A clinical photograph showing a skin lesion; a subject in their 60s.
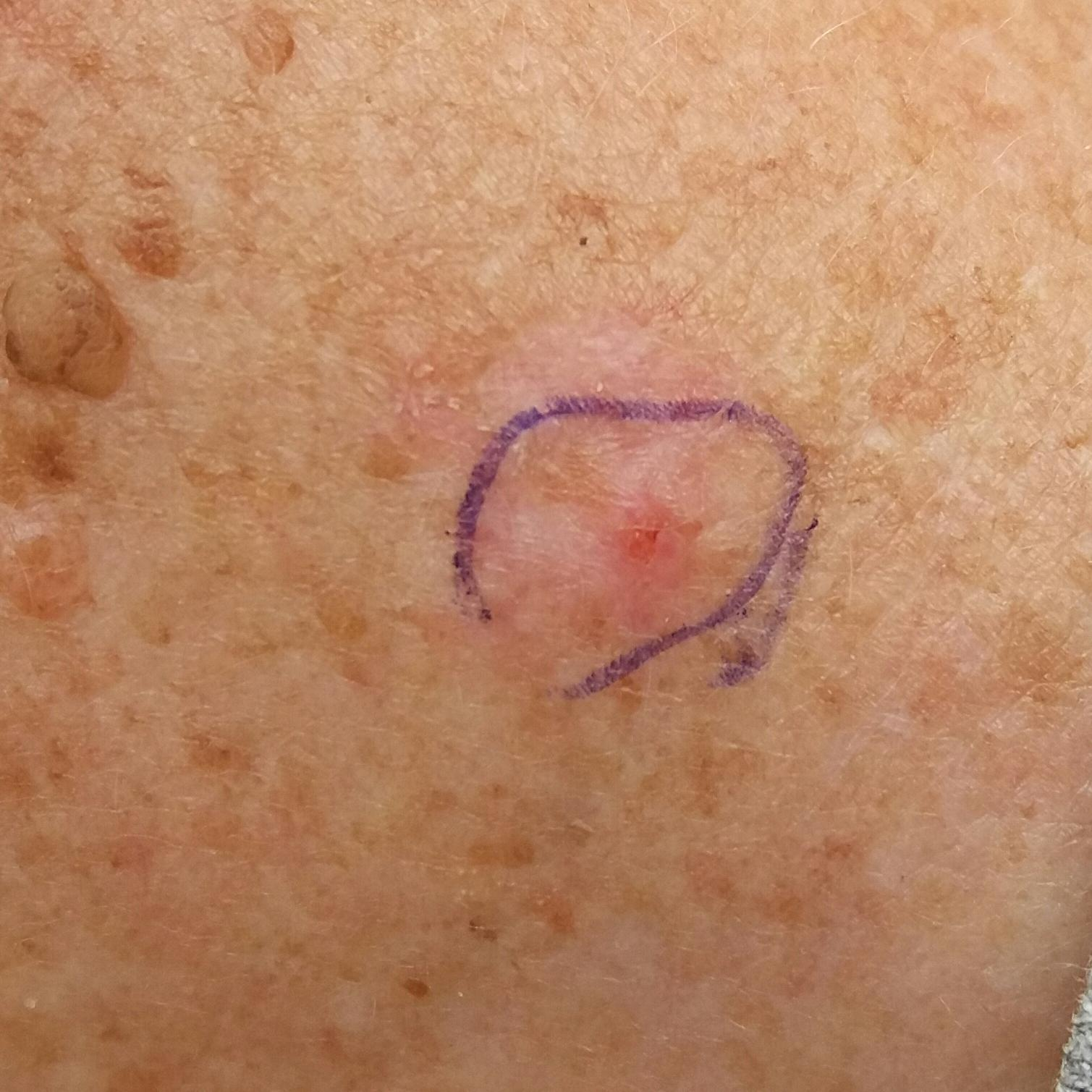Notes:
* body site · the neck
* patient-reported symptoms · itching
* assessment · actinic keratosis (clinical consensus)